Female subject, age 30–39 · the photo was captured at an angle: 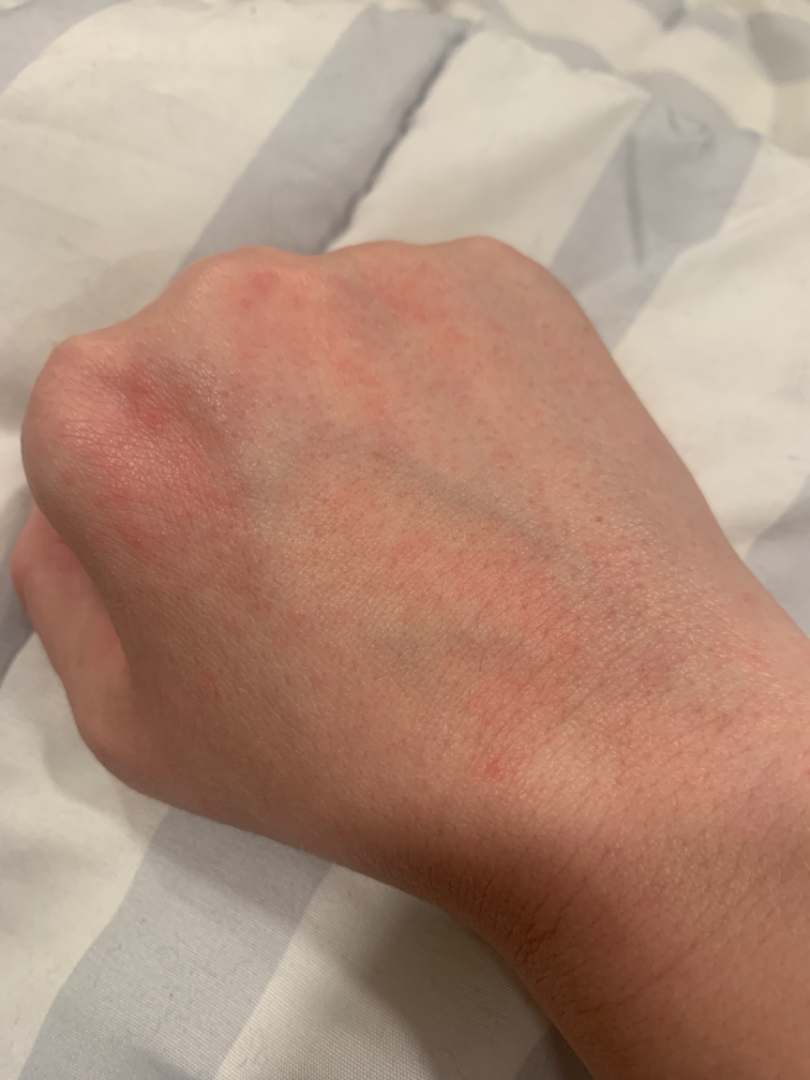differential=Photodermatitis, Allergic Contact Dermatitis and Irritant Contact Dermatitis were each considered, in no particular order.